A dermoscopy image of a single skin lesion: 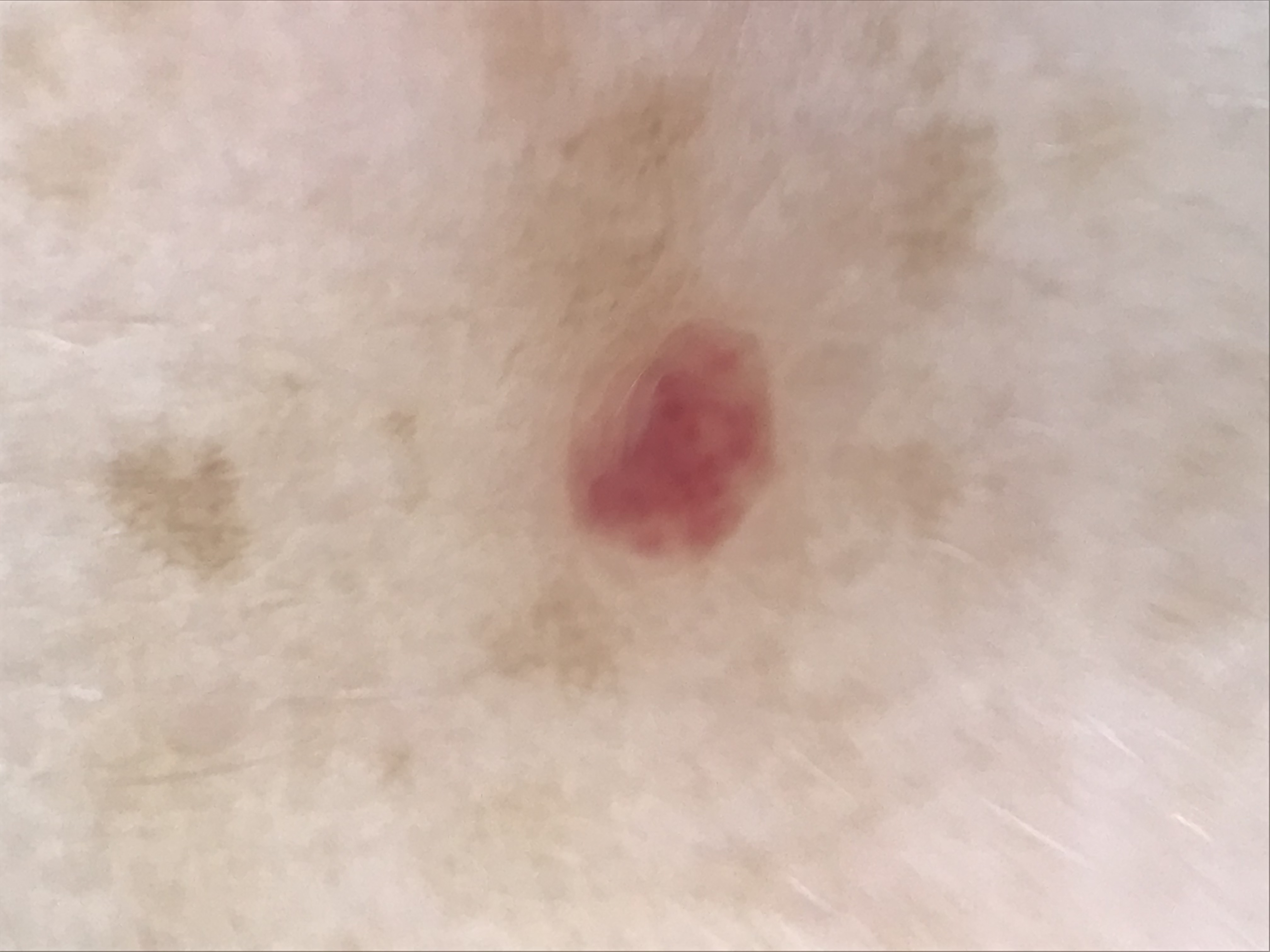Diagnosed as a vascular, benign lesion — a hemangioma.